The patient is a female aged 30–39; a close-up photograph; located on the arm and back of the hand — 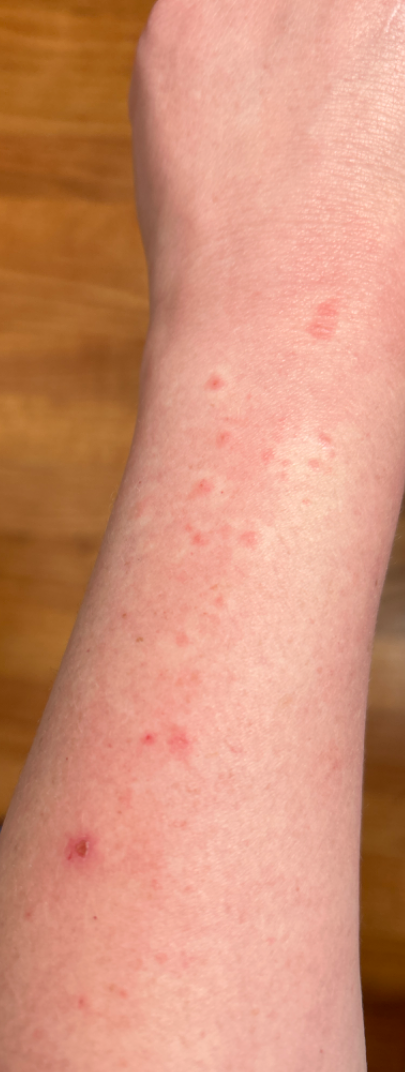- dermatologist impression: Allergic Contact Dermatitis (primary); Urticaria (considered); Insect Bite (considered); Viral Exanthem (less likely); Folliculitis (less likely)